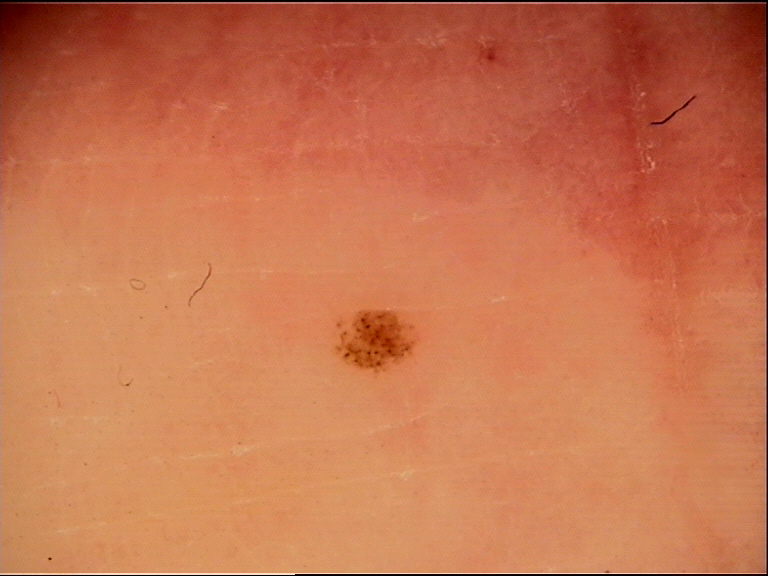Dermoscopy of a skin lesion.
The morphology is that of a banal lesion.
The diagnostic label was an acral junctional nevus.